A male subject, roughly 50 years of age · a skin lesion imaged with a dermatoscope — 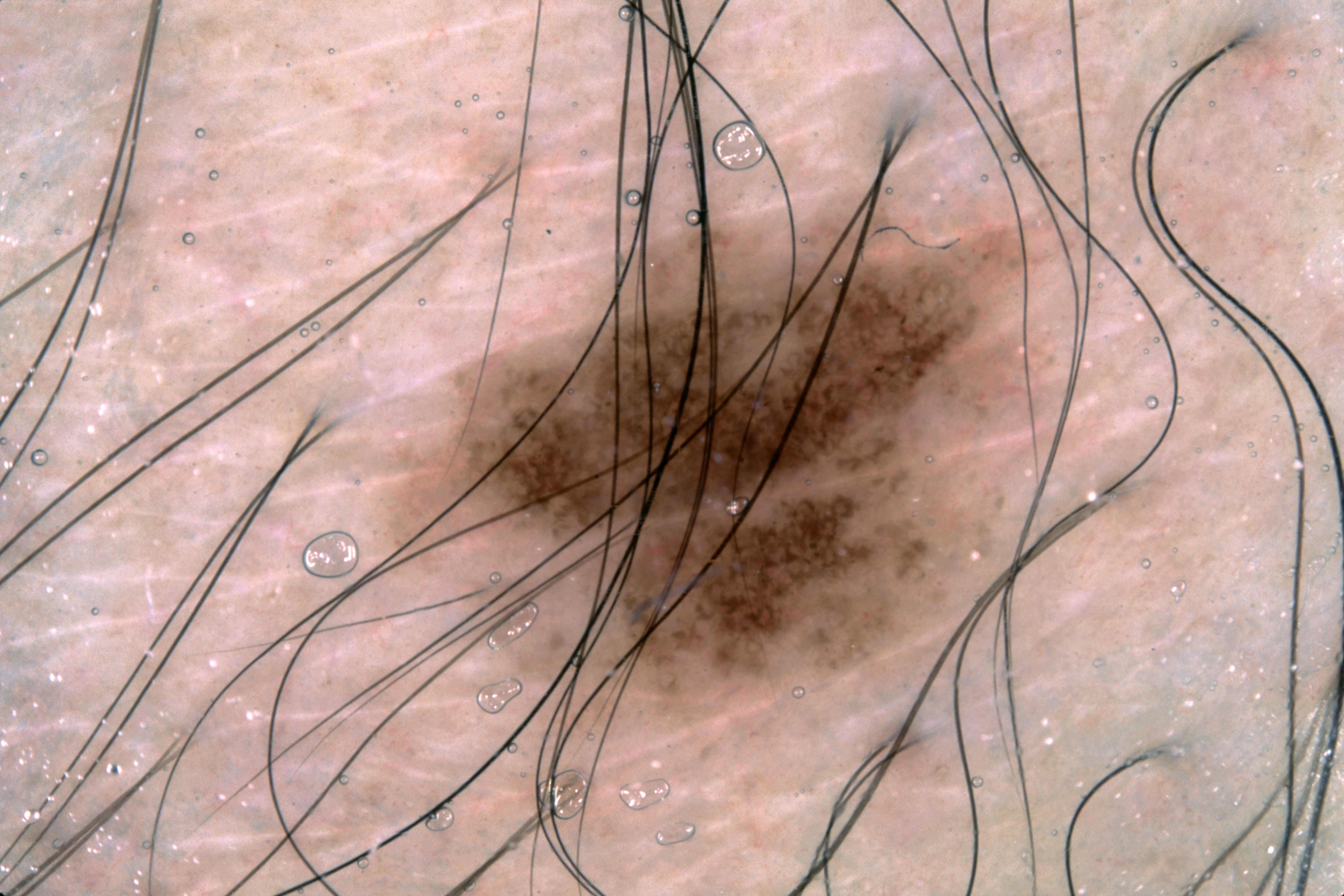lesion location: x1=366, y1=93, x2=1066, y2=795 | dermoscopic features: pigment network | size: ~30% of the field | impression: a melanocytic nevus.